The photograph was taken at an angle — 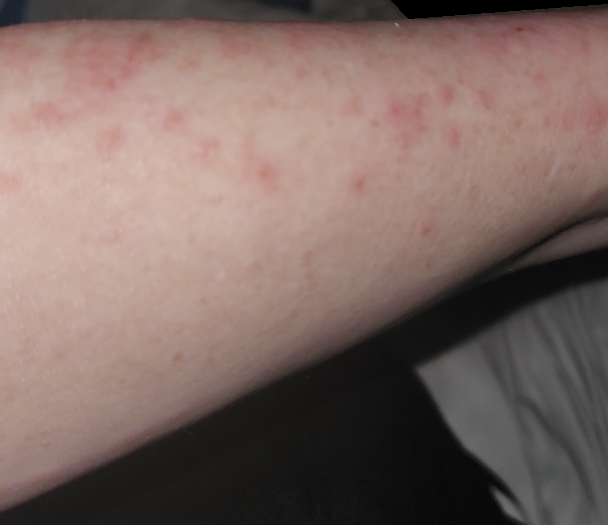Assessment:
Diagnostic features were not clearly distinguishable in this photograph.